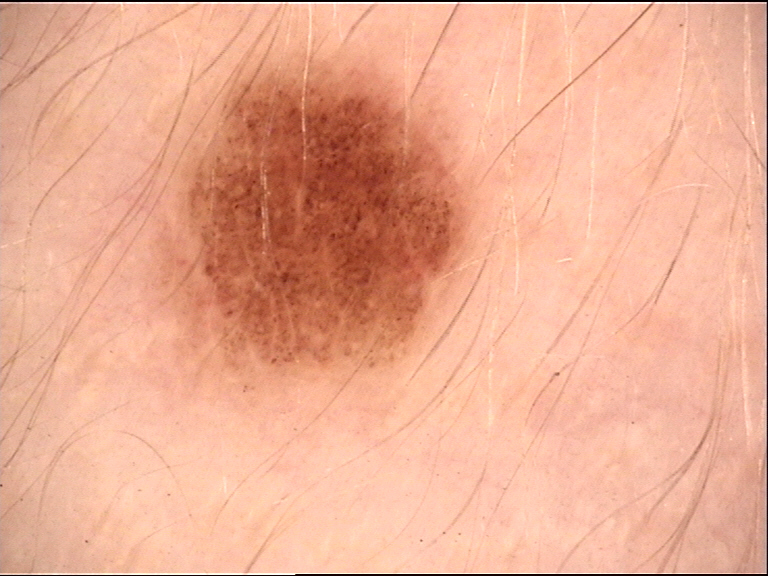A dermoscopy image of a single skin lesion. Classified as a benign lesion — a dysplastic compound nevus.